A close-up photograph; the top or side of the foot is involved; female subject, age 40–49.
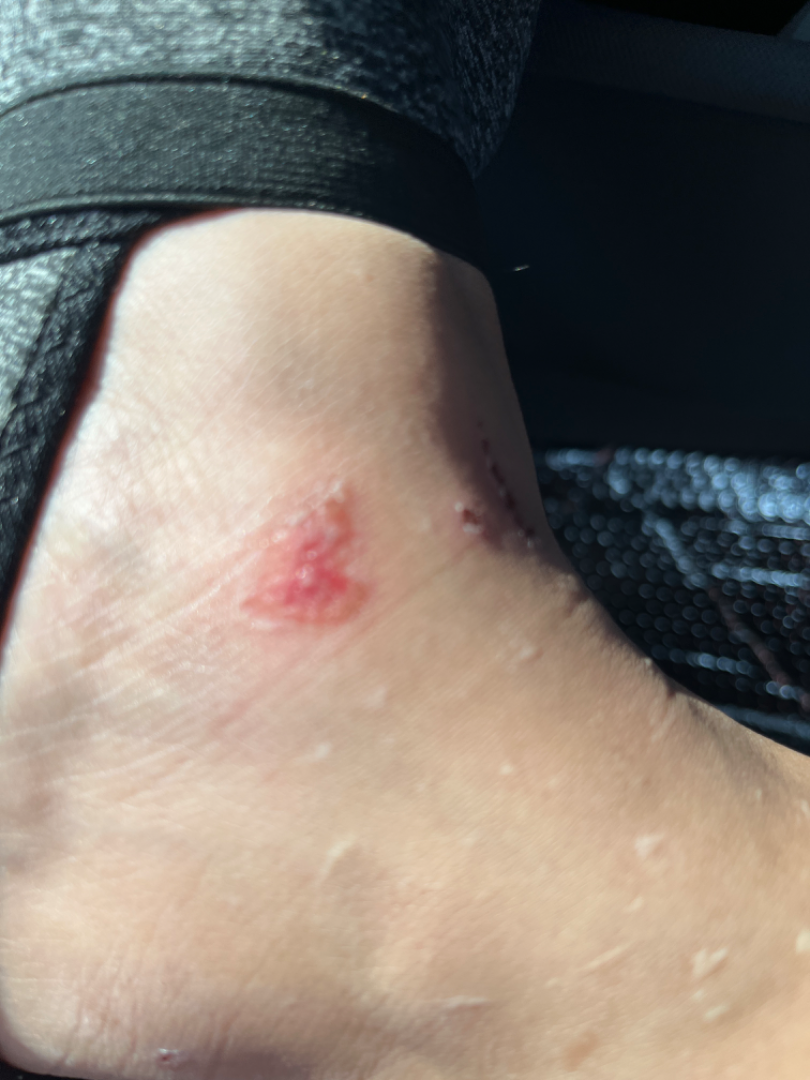Impression: The reviewer was unable to grade this case for skin condition. History: Skin tone: FST III; non-clinician graders estimated Monk Skin Tone 2 or 3. The patient indicates the lesion is fluid-filled. Symptoms reported: burning and itching. The patient indicates the condition has been present for about one day.